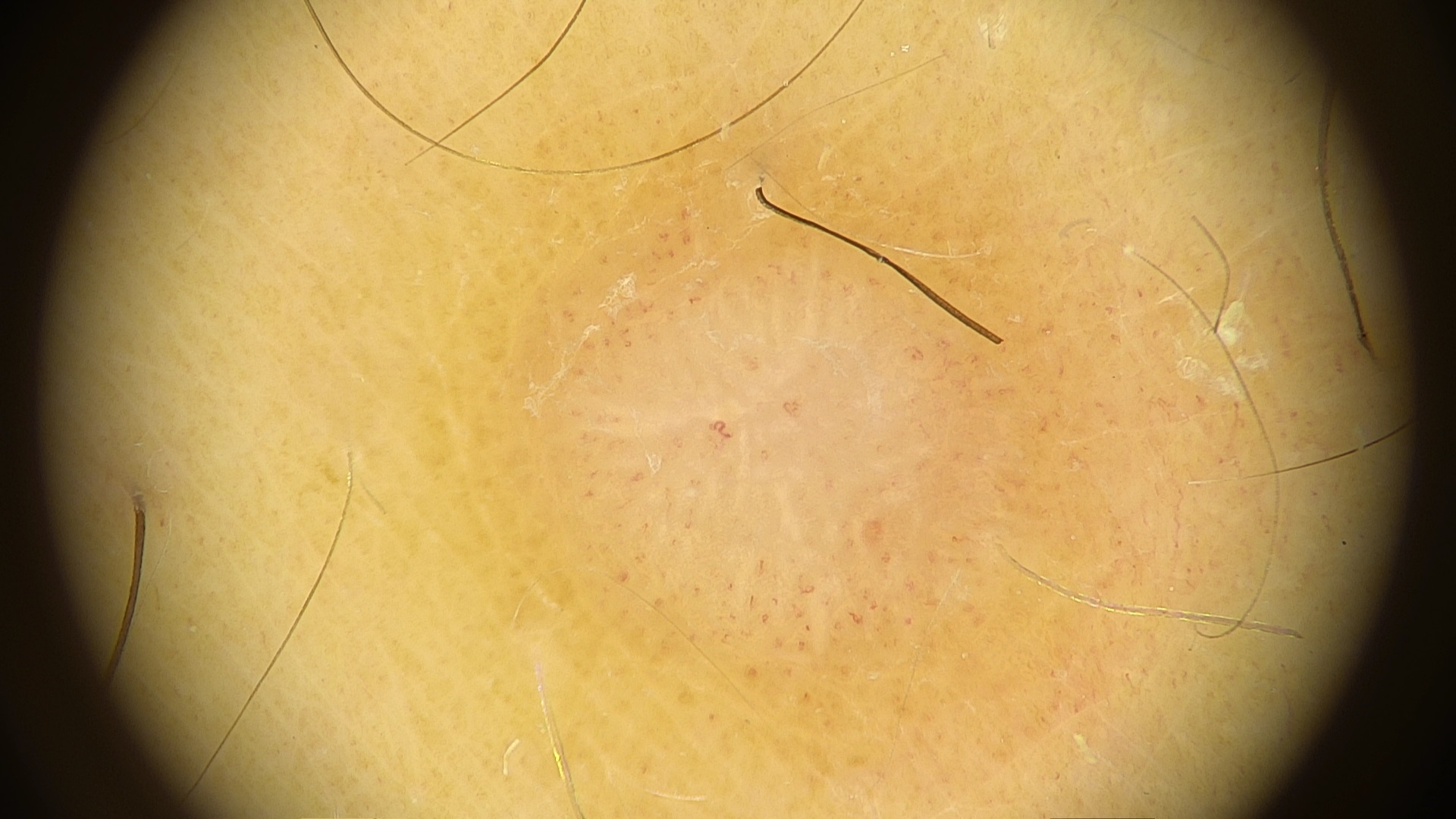The diagnostic label was a fibro-histiocytic lesion — a dermatofibroma.